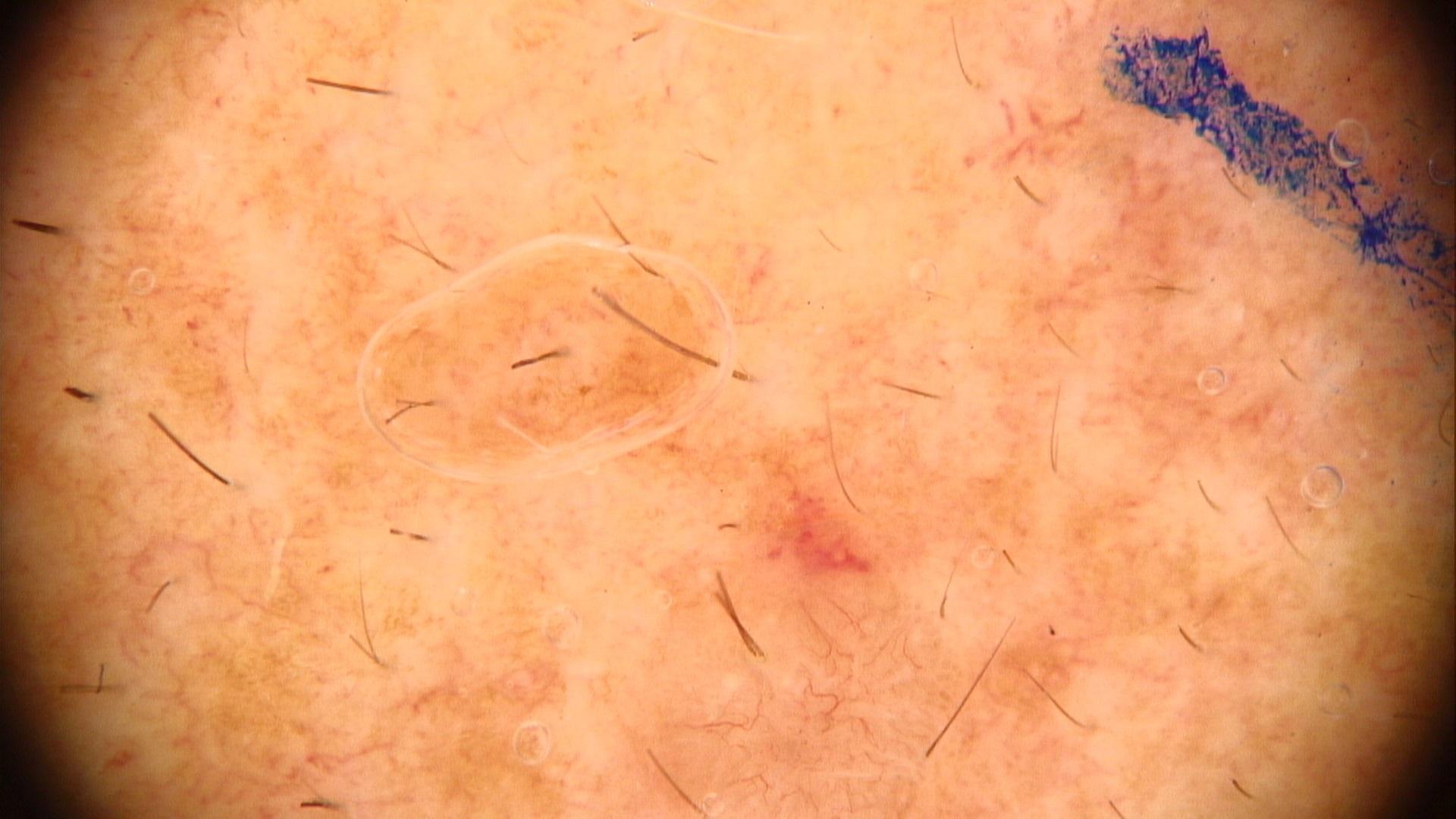A male subject aged approximately 70. The chart records a previous melanoma but no first-degree relative with melanoma. A dermoscopic image of a skin lesion. Recorded as FST II. The lesion is located on the head or neck. On biopsy, the diagnosis was an adnexal lesion — a basal cell carcinoma.